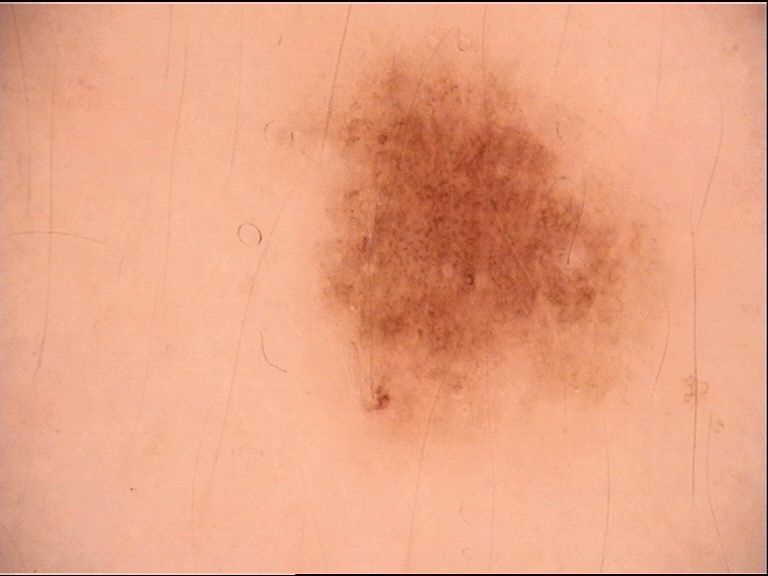Case:
- image — dermoscopy
- assessment — dysplastic junctional nevus (expert consensus)